The photo was captured at a distance: 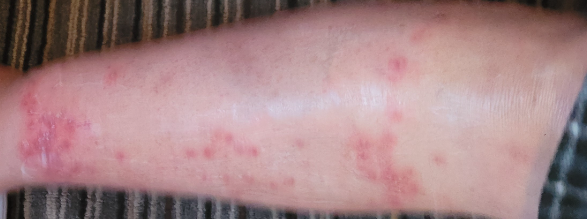Case summary:
• skin tone · lay reviewers estimated Monk skin tone scale 2–3
• differential diagnosis · Insect Bite (weight 1.00)